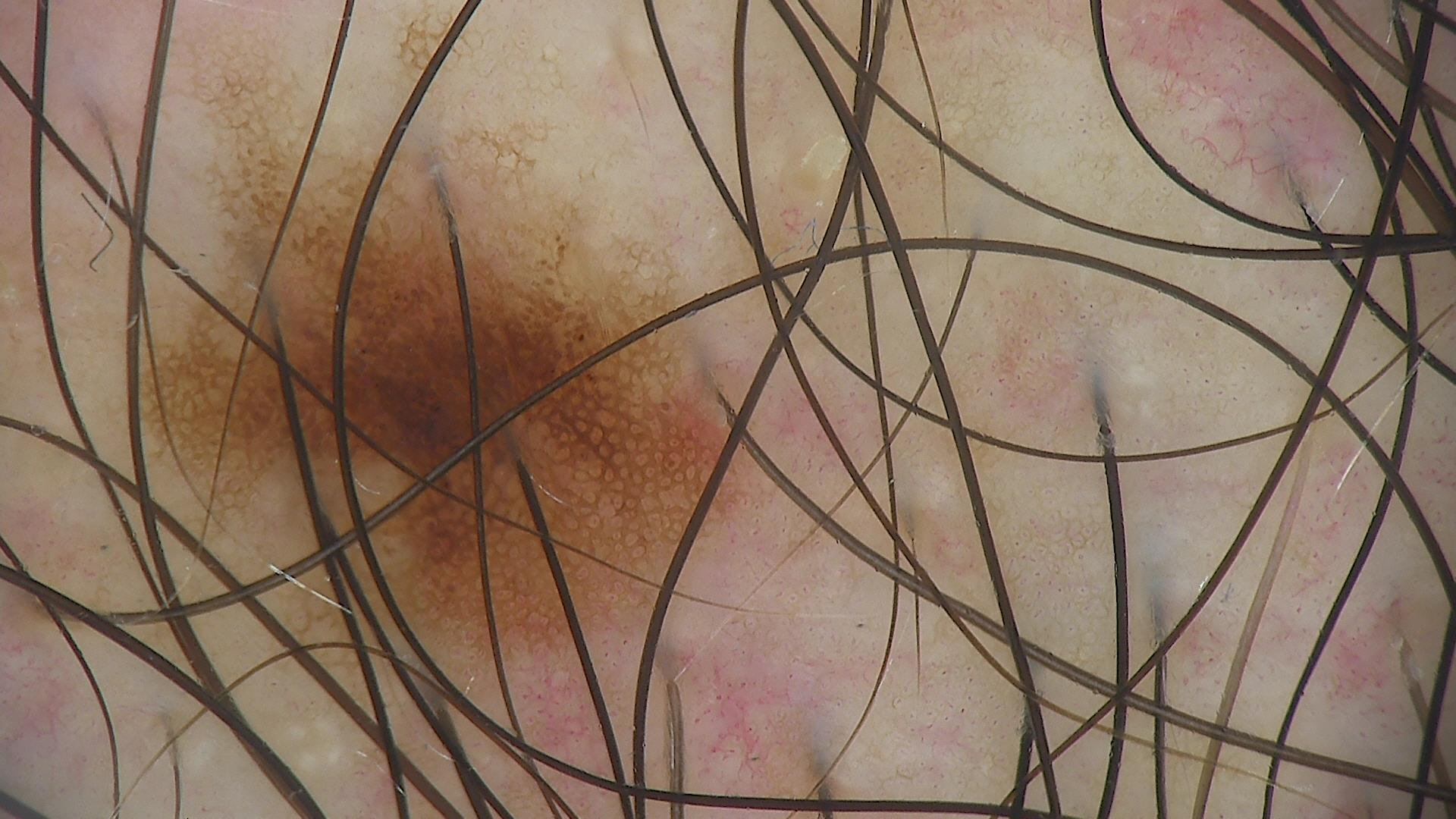Q: What kind of image is this?
A: dermatoscopy
Q: What is the diagnosis?
A: dysplastic junctional nevus (expert consensus)